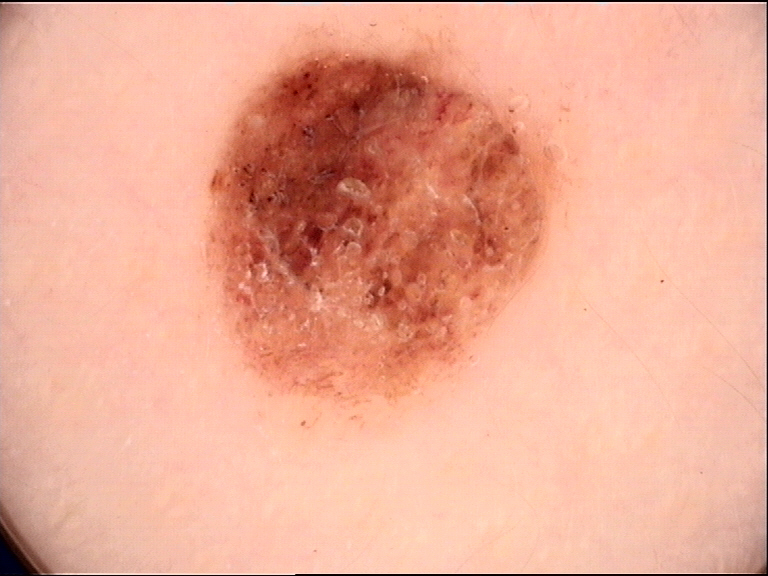Findings: A dermoscopic photograph of a skin lesion. Conclusion: Diagnosed as a benign lesion — a dysplastic compound nevus.